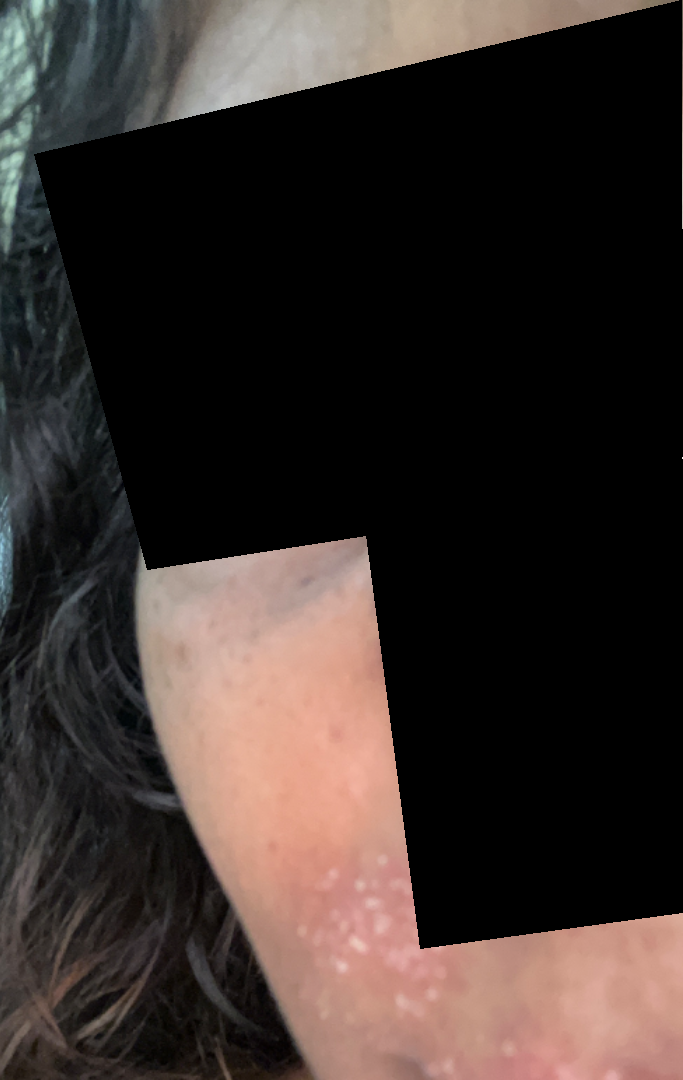<case>
<shot_type>at an angle</shot_type>
<differential>
  <tied_lead>Acne, Milia, Perioral Dermatitis</tied_lead>
</differential>
</case>